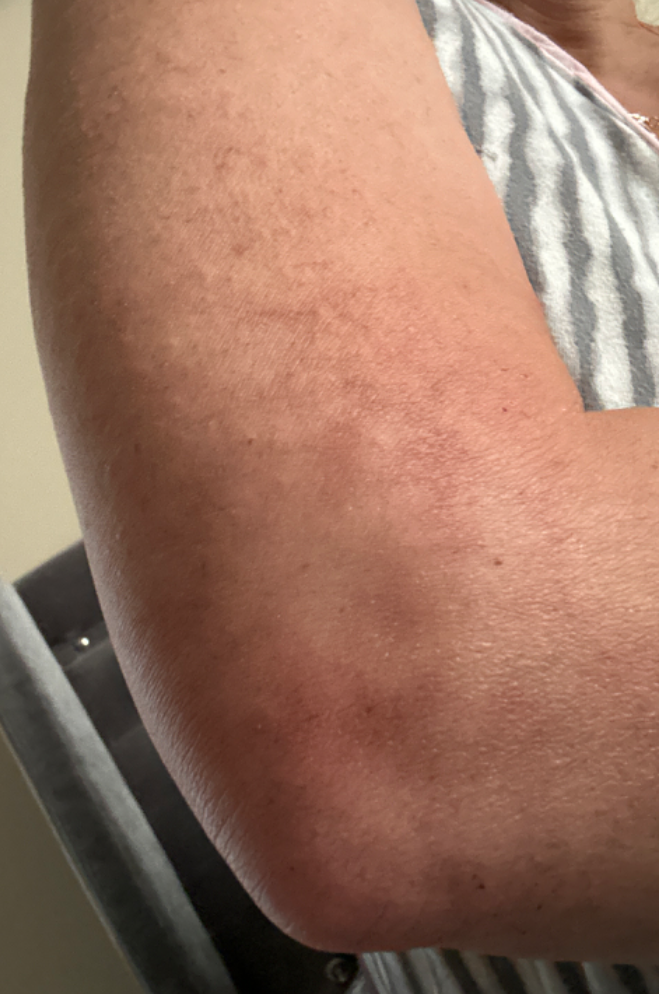Impression:
The case was difficult to assess from the available photograph.
History:
The photograph was taken at an angle.